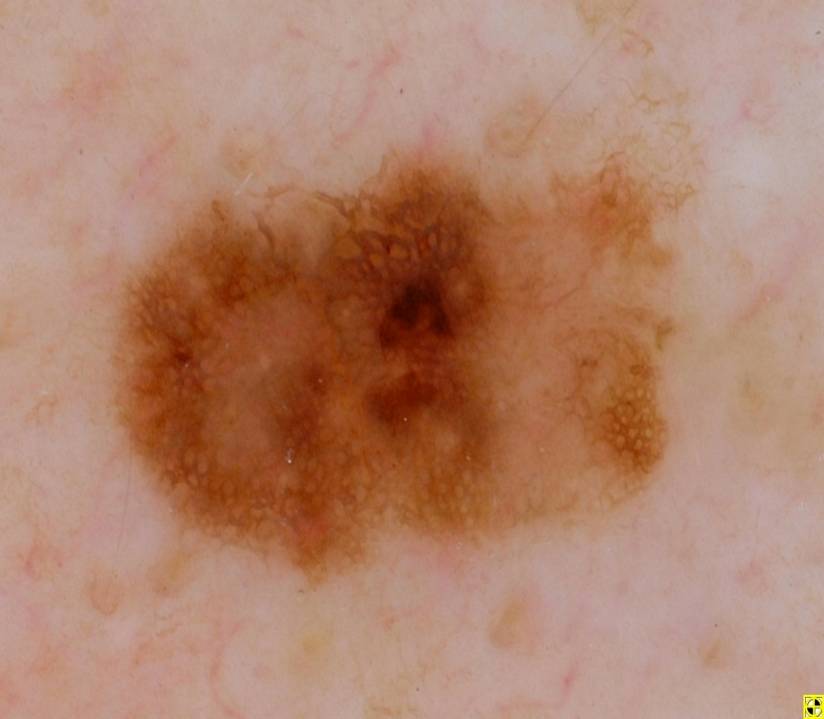A dermoscopic view of a skin lesion.
The lesion takes up a large portion of the image.
On dermoscopy, the lesion shows pigment network.
As (left, top, right, bottom), the lesion is bounded by [110,151,676,586].
Diagnosed as a melanocytic nevus.